History notes prior skin cancer (patient or family); a clinical photo of a skin lesion taken with a smartphone; the patient was assessed as Fitzpatrick phototype III:
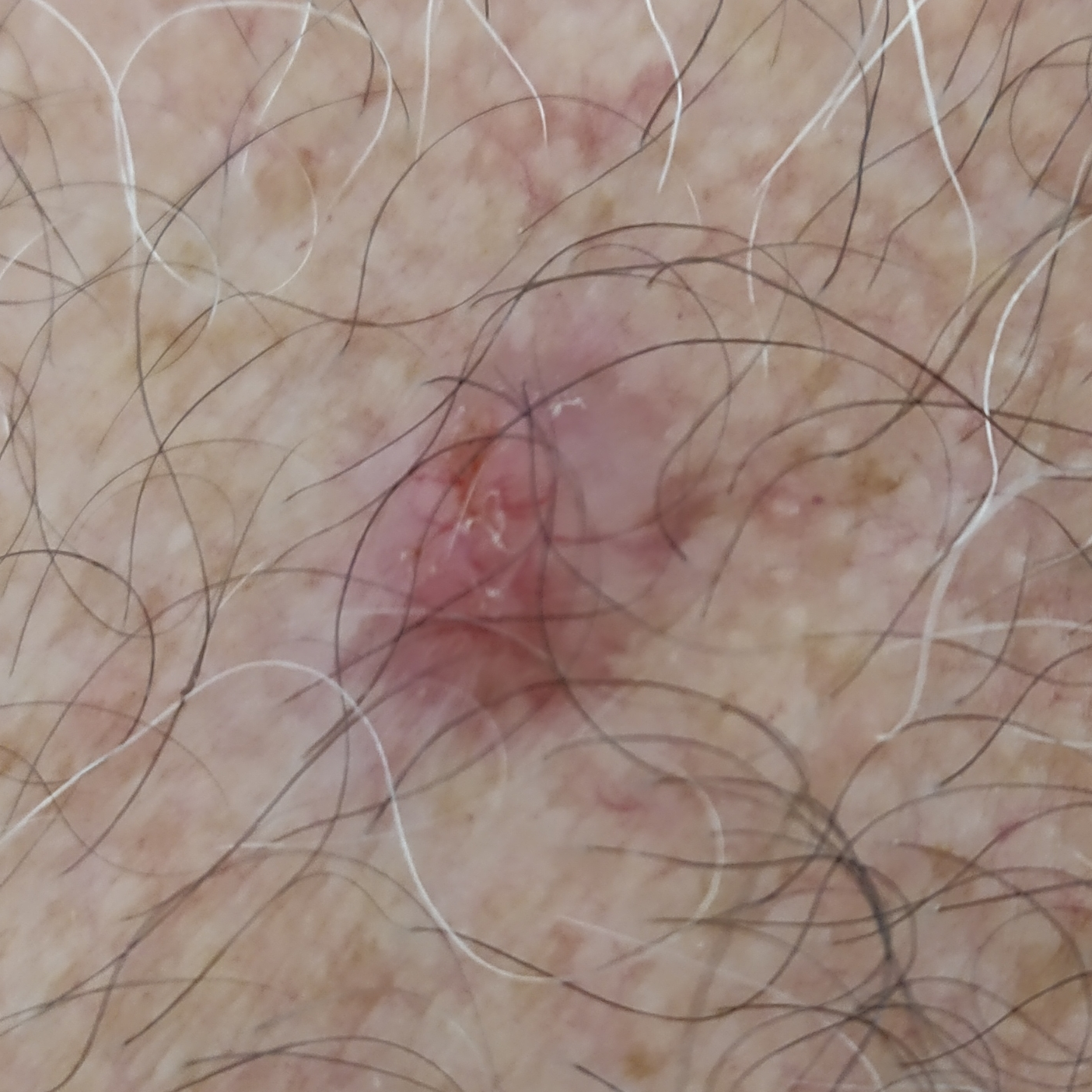{
  "lesion_size": {
    "diameter_1_mm": 13.0,
    "diameter_2_mm": 12.0
  },
  "symptoms": {
    "present": [
      "elevation",
      "itching",
      "growth"
    ]
  },
  "diagnosis": {
    "name": "basal cell carcinoma",
    "code": "BCC",
    "malignancy": "malignant",
    "confirmation": "histopathology"
  }
}